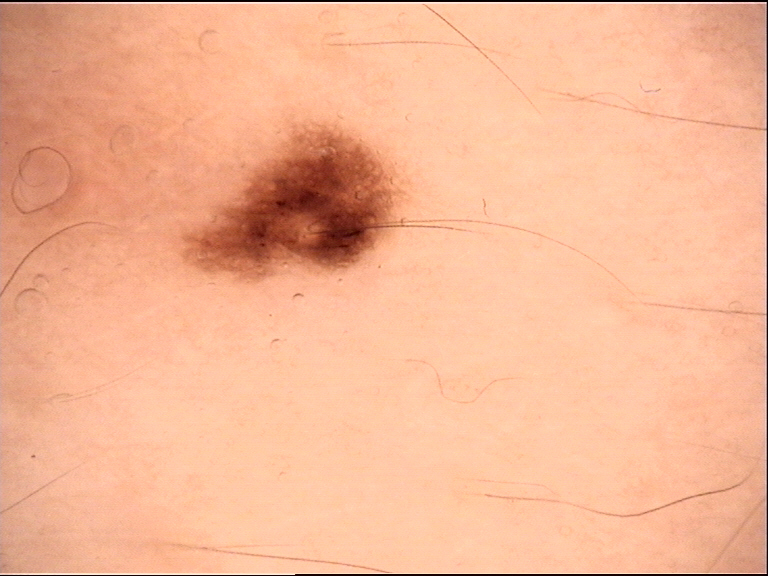A dermoscopic photograph of a skin lesion. Classified as a dysplastic junctional nevus.